A dermoscopic image of a skin lesion.
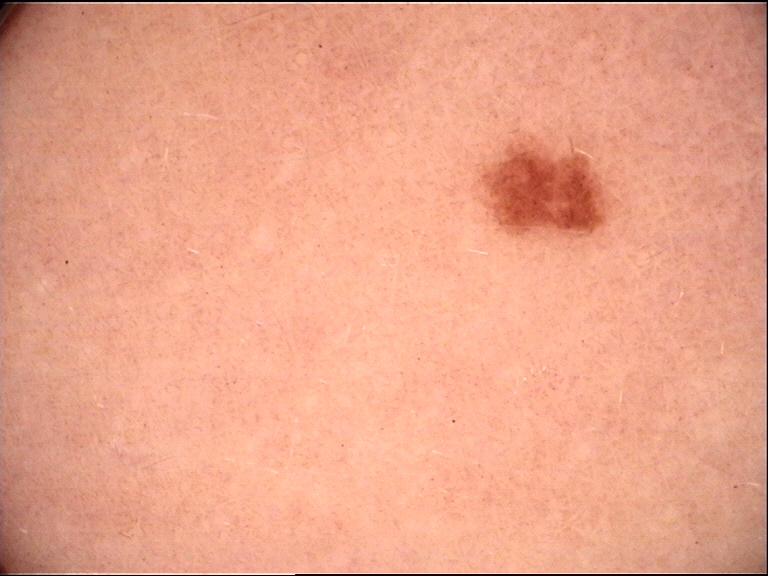label = dysplastic junctional nevus (expert consensus).